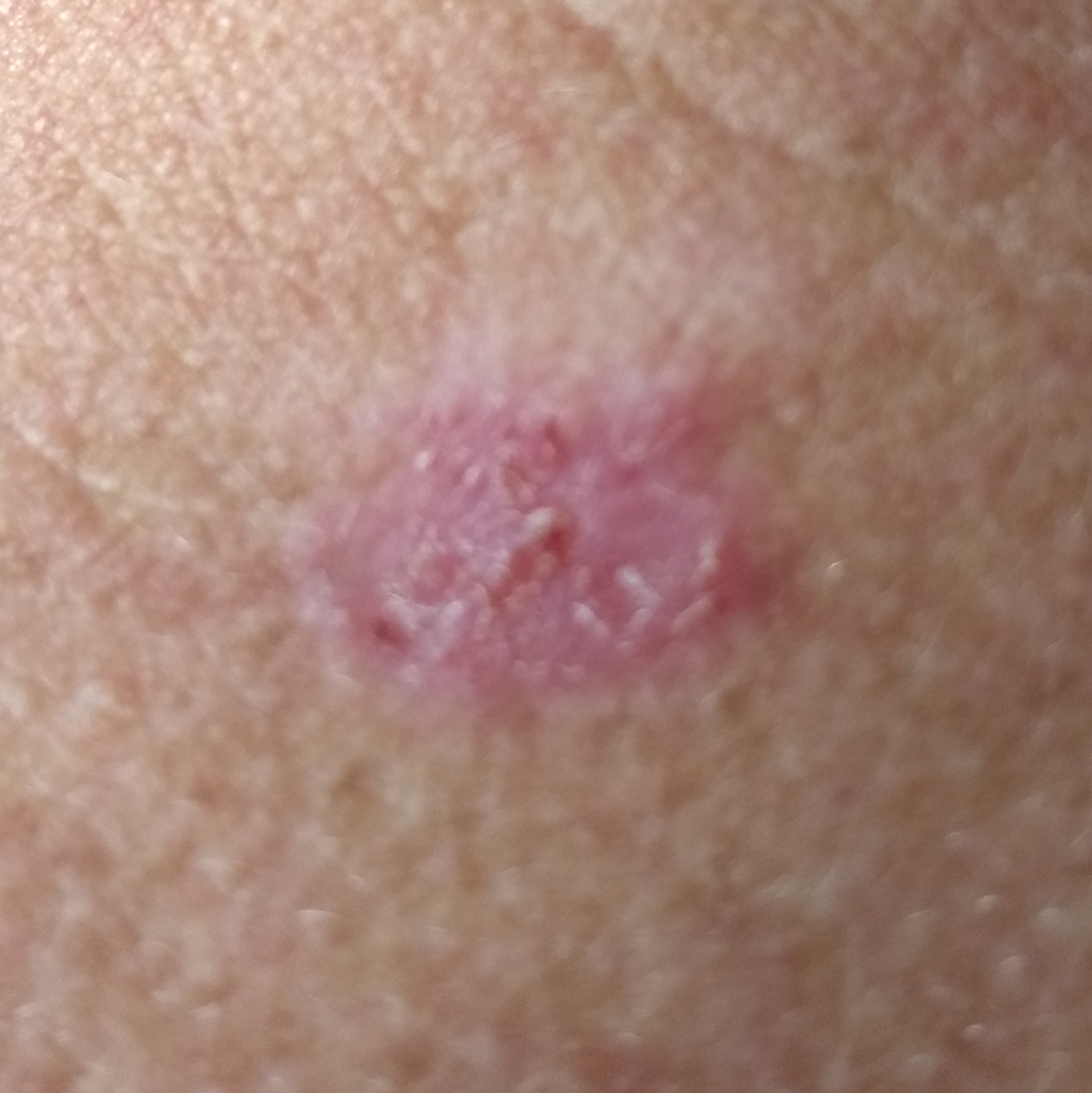Case summary: A clinical photograph showing a skin lesion. A female patient in their late 30s. The patient is Fitzpatrick phototype II. The chart records prior skin cancer (patient or family), prior malignancy (patient or family), pesticide exposure, no alcohol use, and no tobacco use. Located on the neck. The lesion is roughly 13 by 10 mm. The patient describes that the lesion has grown, itches, and has bled, but has not changed. Pathology: Biopsy-confirmed as a basal cell carcinoma.